A female subject about 50 years old, a dermoscopic image of a skin lesion:
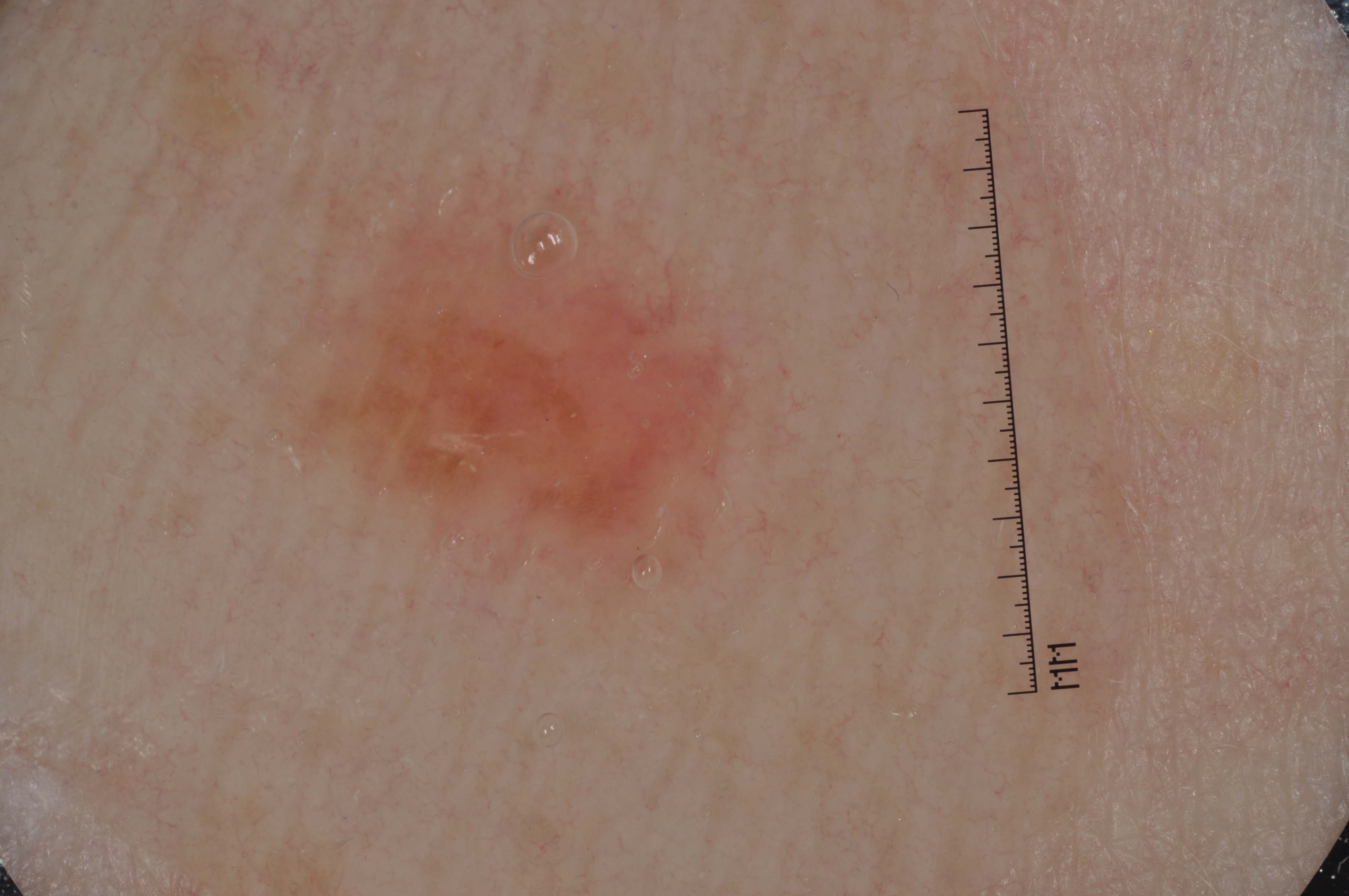Q: Where is the lesion in the image?
A: x1=274, y1=175, x2=748, y2=595
Q: How much of the field does the lesion occupy?
A: ~12% of the field
Q: Which dermoscopic features were noted?
A: milia-like cysts
Q: What is the diagnosis?
A: a melanocytic nevus